The patient indicates bothersome appearance and itching; reported duration is one to three months; no constitutional symptoms were reported; the affected area is the arm; the lesion is described as raised or bumpy and rough or flaky; the patient considered this a rash; the patient is female; the photograph is a close-up of the affected area: 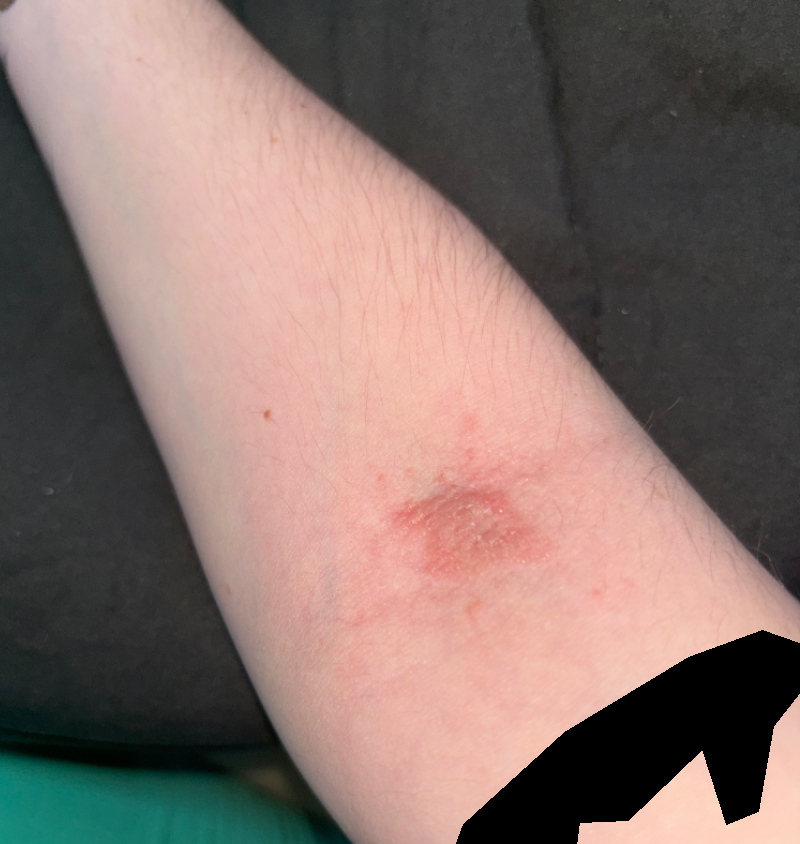{"differential": {"tied_lead": ["Eczema", "Allergic Contact Dermatitis"], "unlikely": ["Infected eczema"]}}